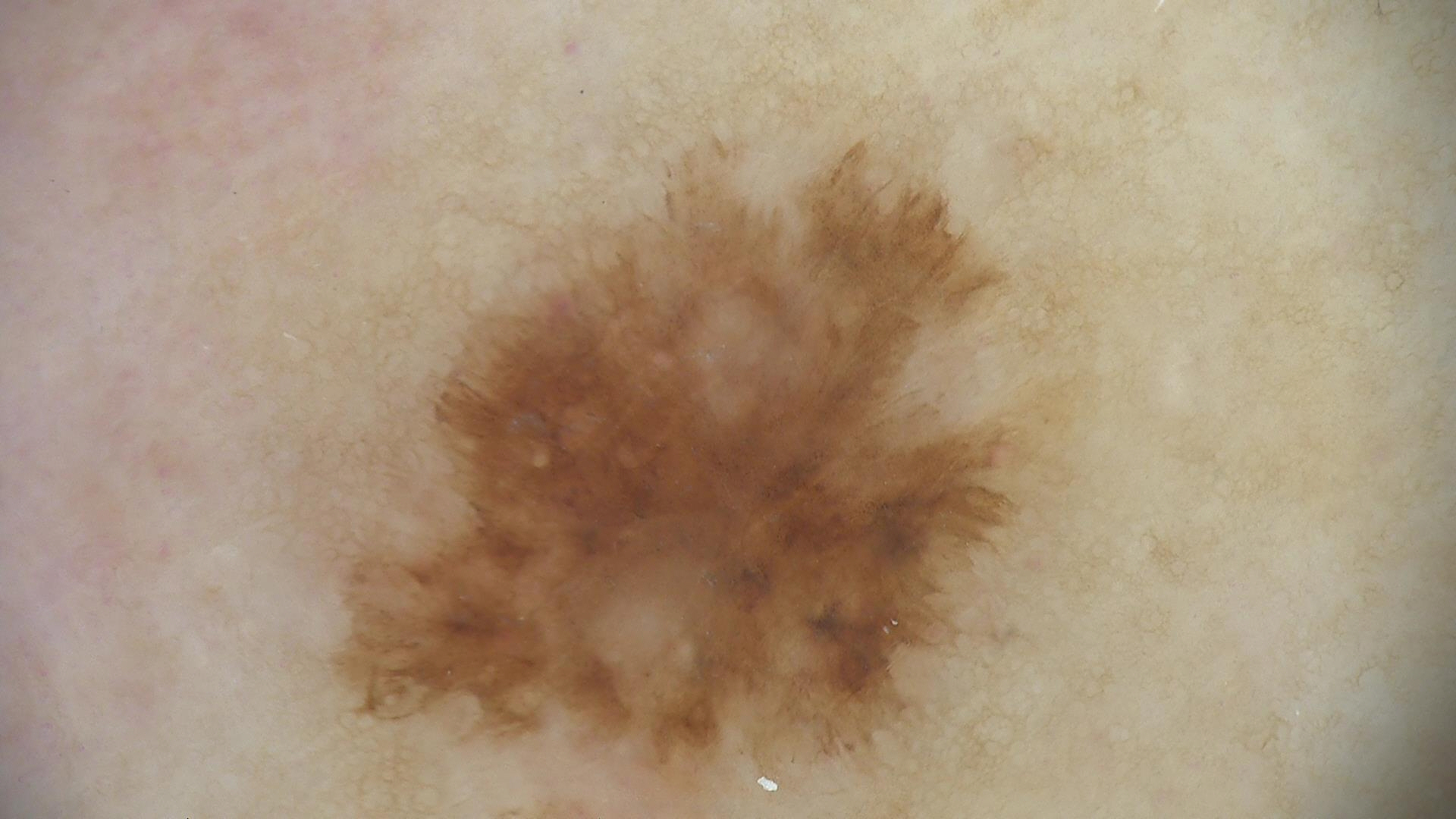Q: What did the workup show?
A: basal cell carcinoma (biopsy-proven)